A dermoscopic image of a skin lesion.
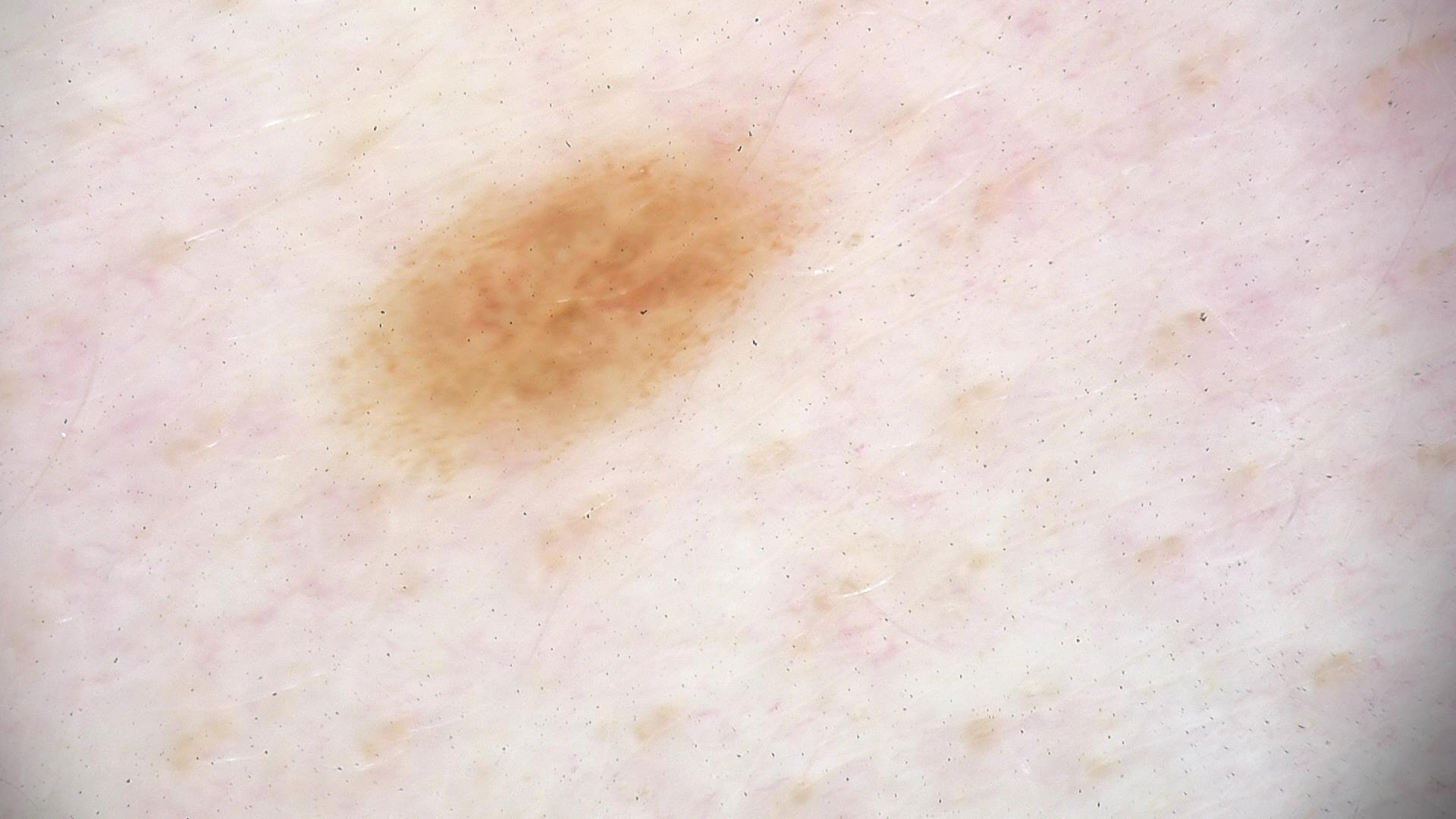Diagnosed as a benign lesion — a dysplastic junctional nevus.